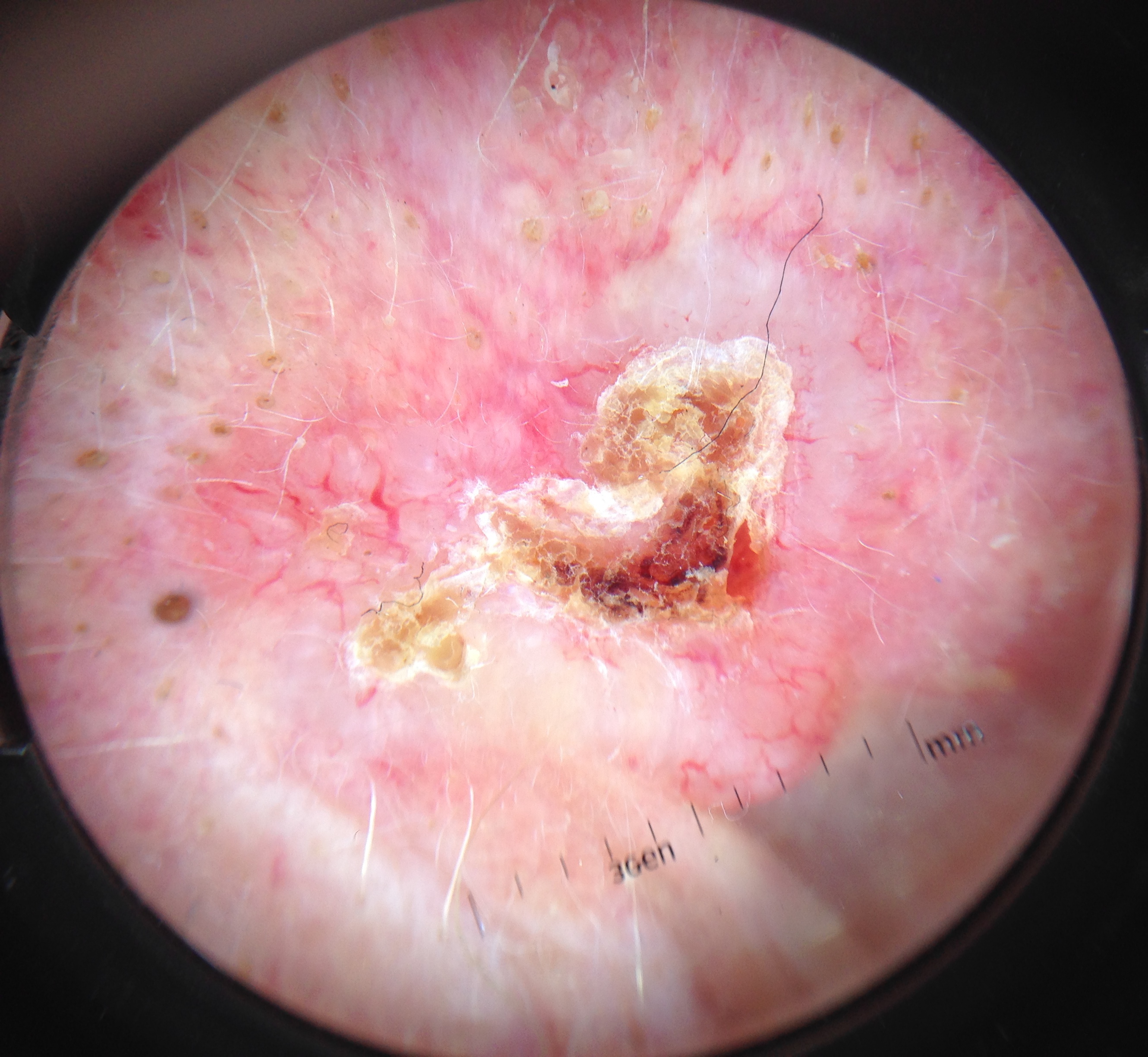imaging = dermatoscopy | subtype = keratinocytic | diagnostic label = basal cell carcinoma (biopsy-proven).